The back of the torso, head or neck and front of the torso are involved; this is a close-up image; self-categorized by the patient as a rash; the condition has been present for one to four weeks; the lesion is described as raised or bumpy and rough or flaky; the patient also reports shortness of breath, joint pain, chills and fatigue: 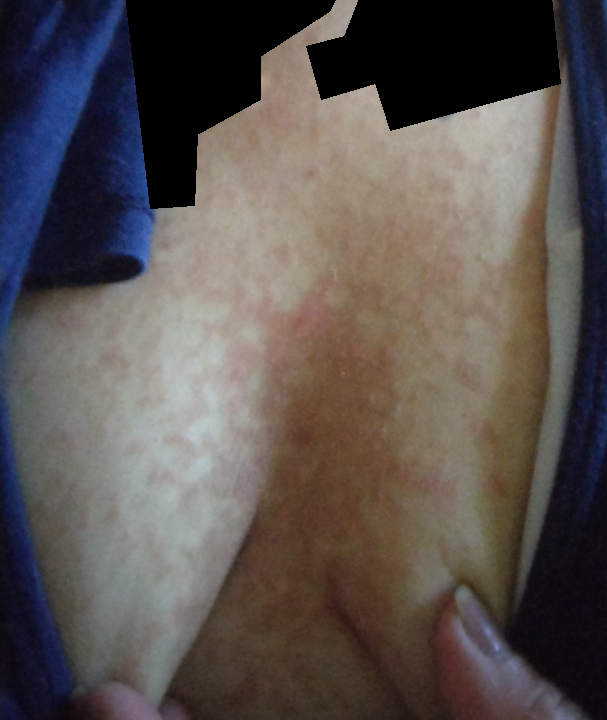The skin findings could not be characterized from the image.